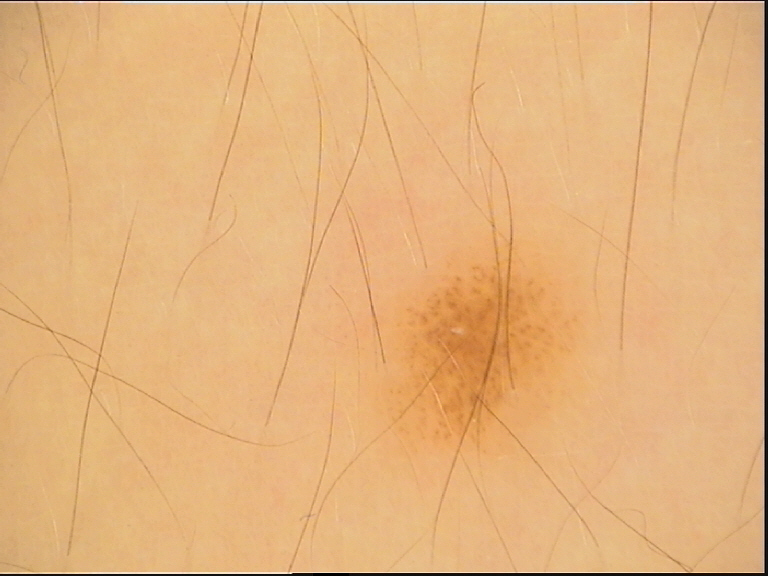A dermoscopy image of a single skin lesion. The diagnostic label was a banal lesion — a junctional nevus.